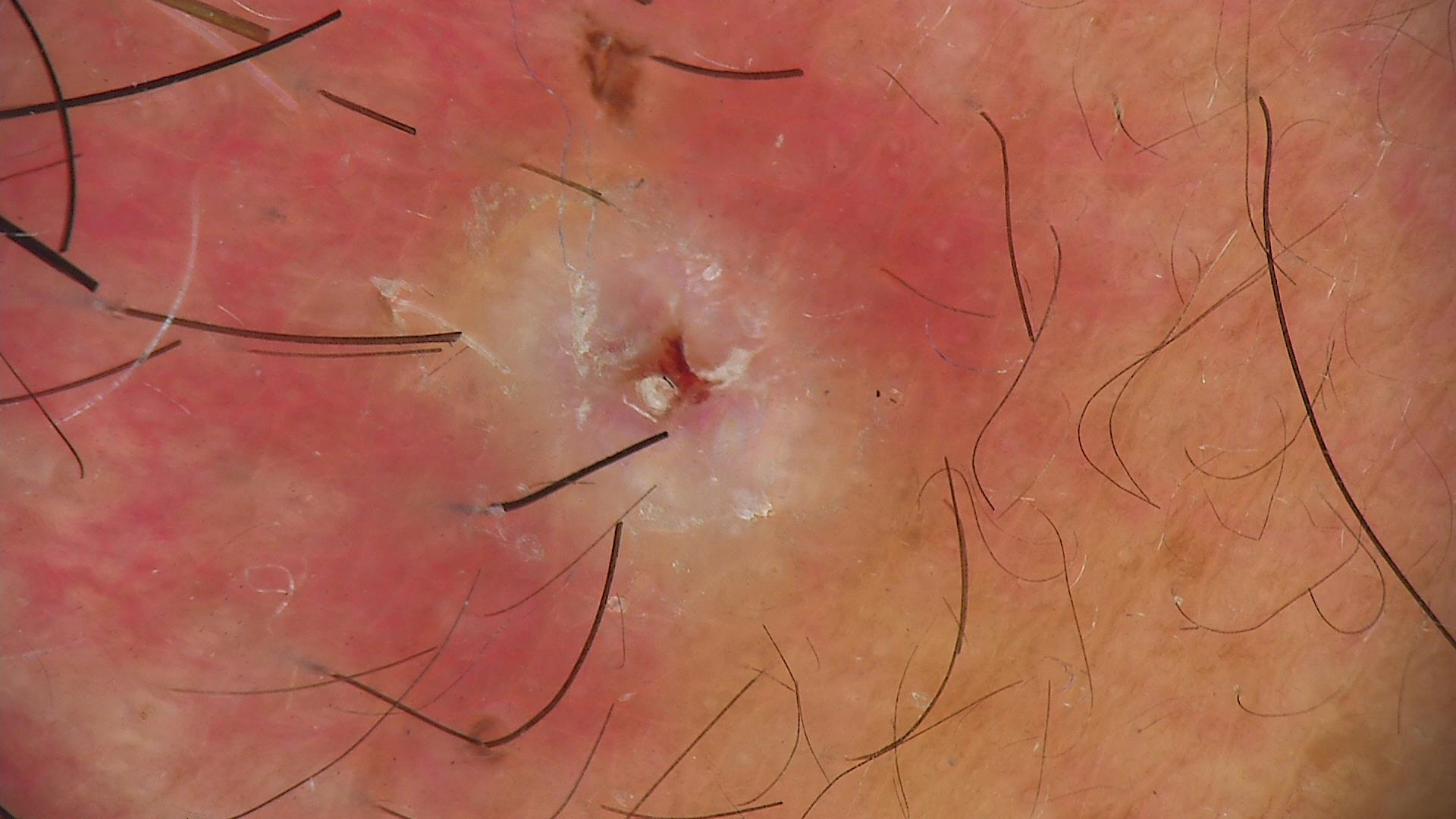Diagnosis: Histopathology confirmed a basal cell carcinoma.